The photo was captured at an angle. The contributor is a male aged 60–69. The lesion involves the leg: 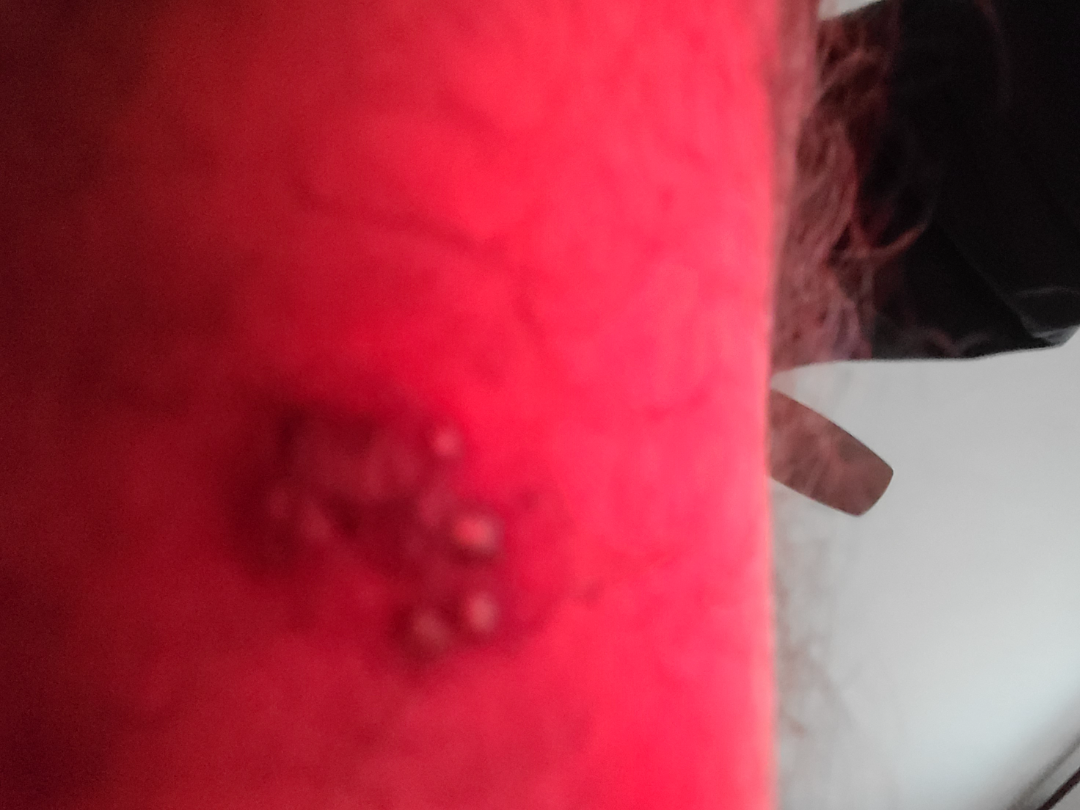{"assessment": "unable to determine"}